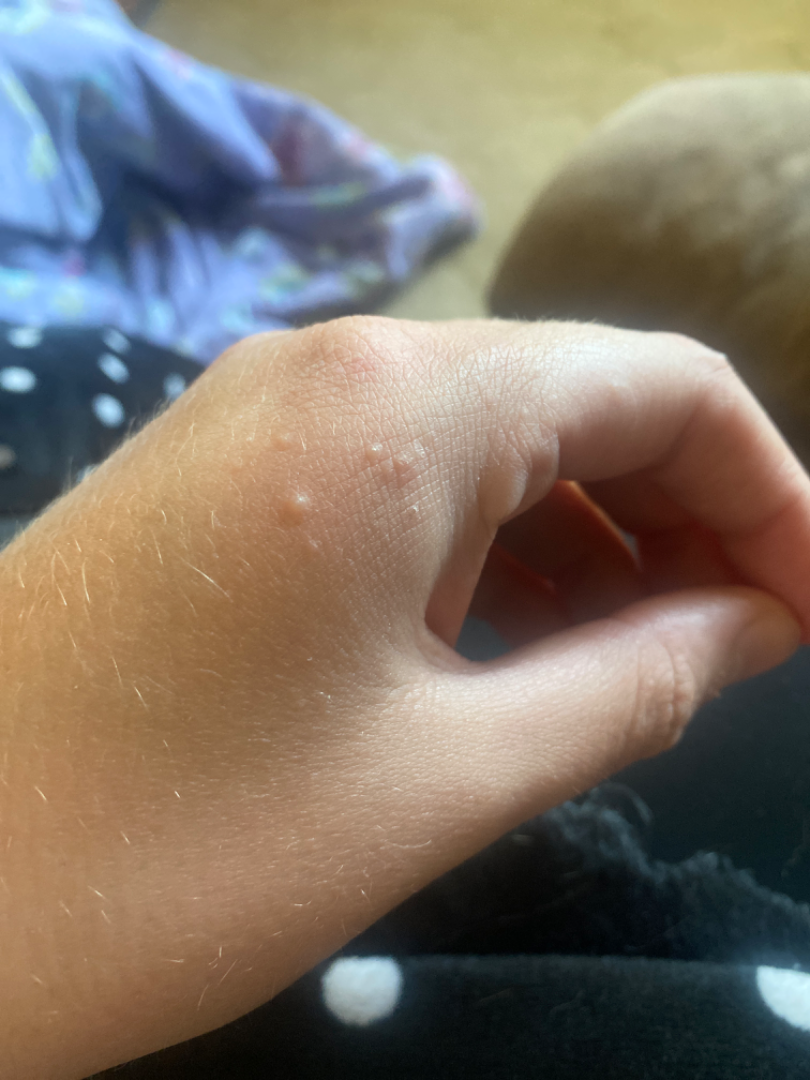{
  "assessment": "could not be assessed"
}